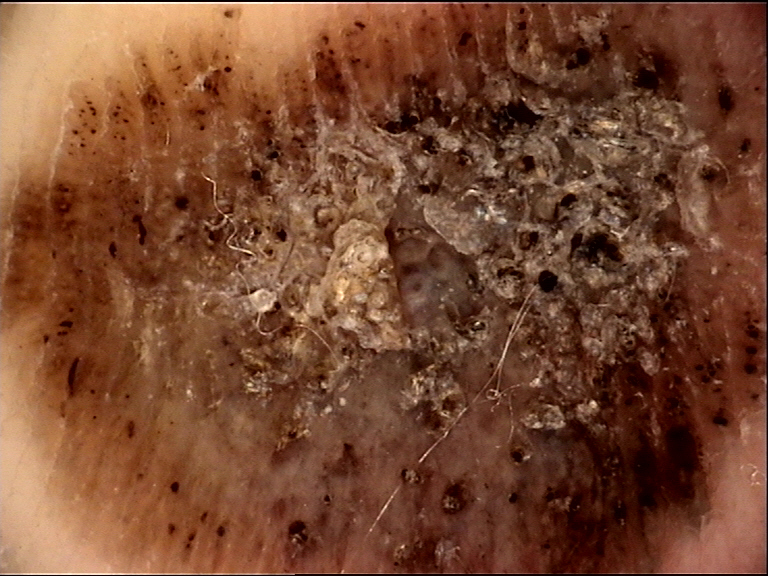Findings:
A skin lesion imaged with a dermatoscope.
Conclusion:
Histopathologically confirmed as an acral nodular melanoma.